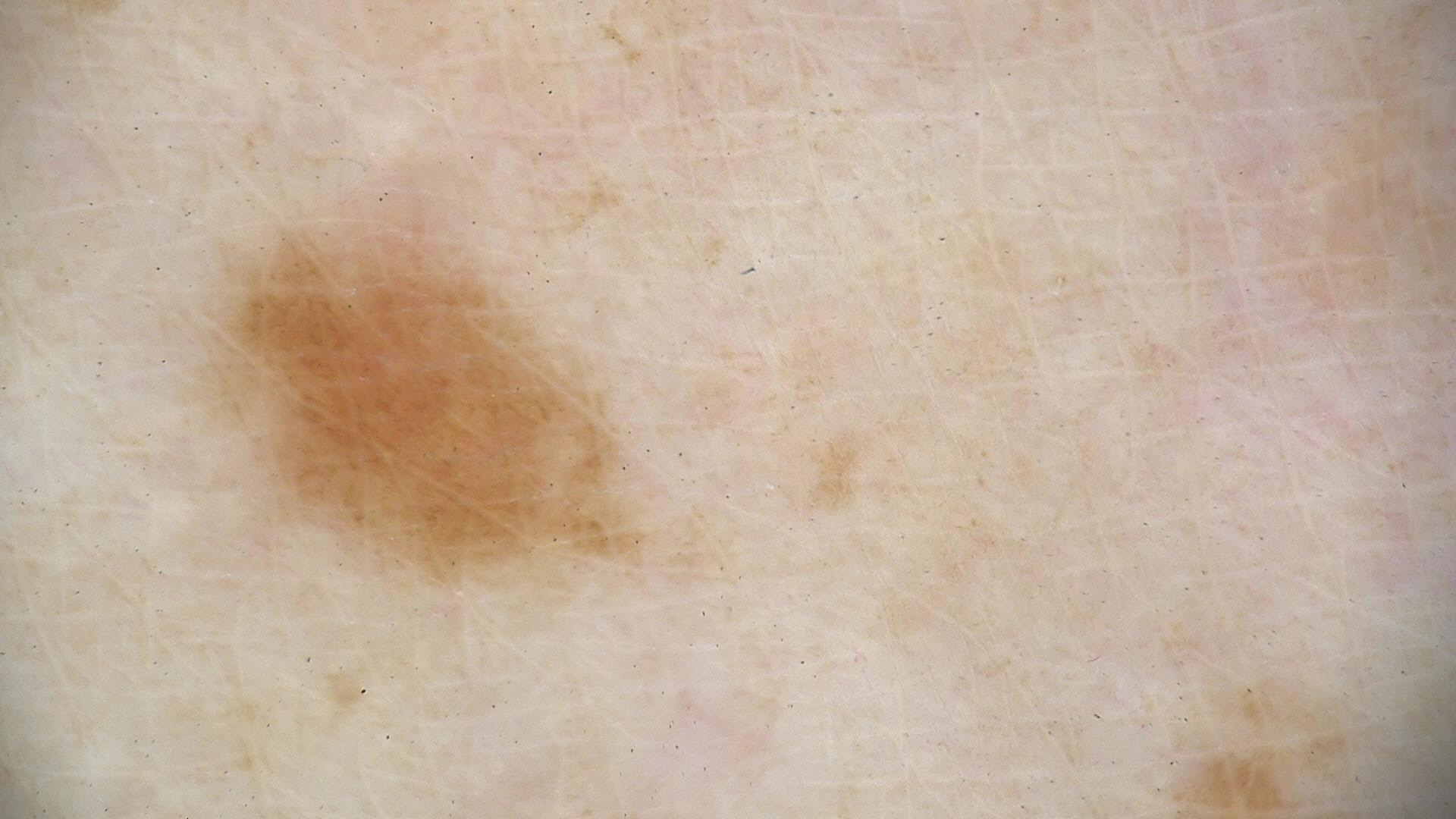Conclusion:
Diagnosed as a lentigo simplex.